A clinical close-up photograph of a skin lesion · a male subject age 75 · history notes alcohol use, prior malignancy (patient or family), and prior skin cancer (patient or family) · the patient was assessed as FST II: 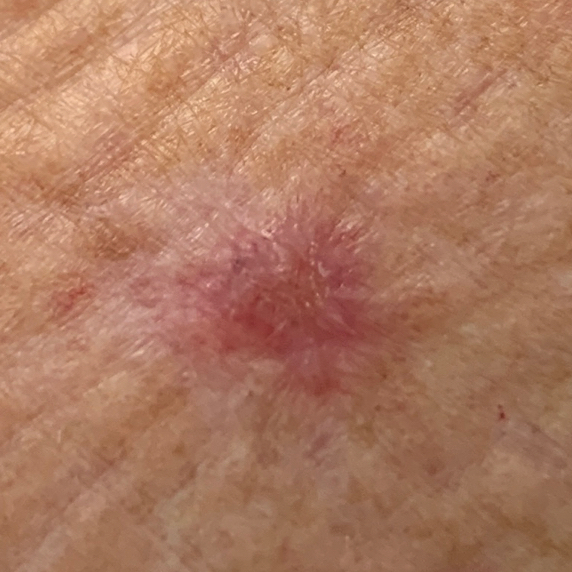{"lesion_location": "an arm", "lesion_size": {"diameter_1_mm": 8.0, "diameter_2_mm": 7.0}, "symptoms": {"present": ["elevation", "itching"], "absent": ["bleeding", "pain"]}, "diagnosis": {"name": "basal cell carcinoma", "code": "BCC", "malignancy": "malignant", "confirmation": "histopathology"}}